A female patient 70 years of age; the chart notes prior malignancy (patient or family), tobacco use, no prior skin cancer (patient or family), and no alcohol use; a clinical photograph of a skin lesion; the patient is FST II — 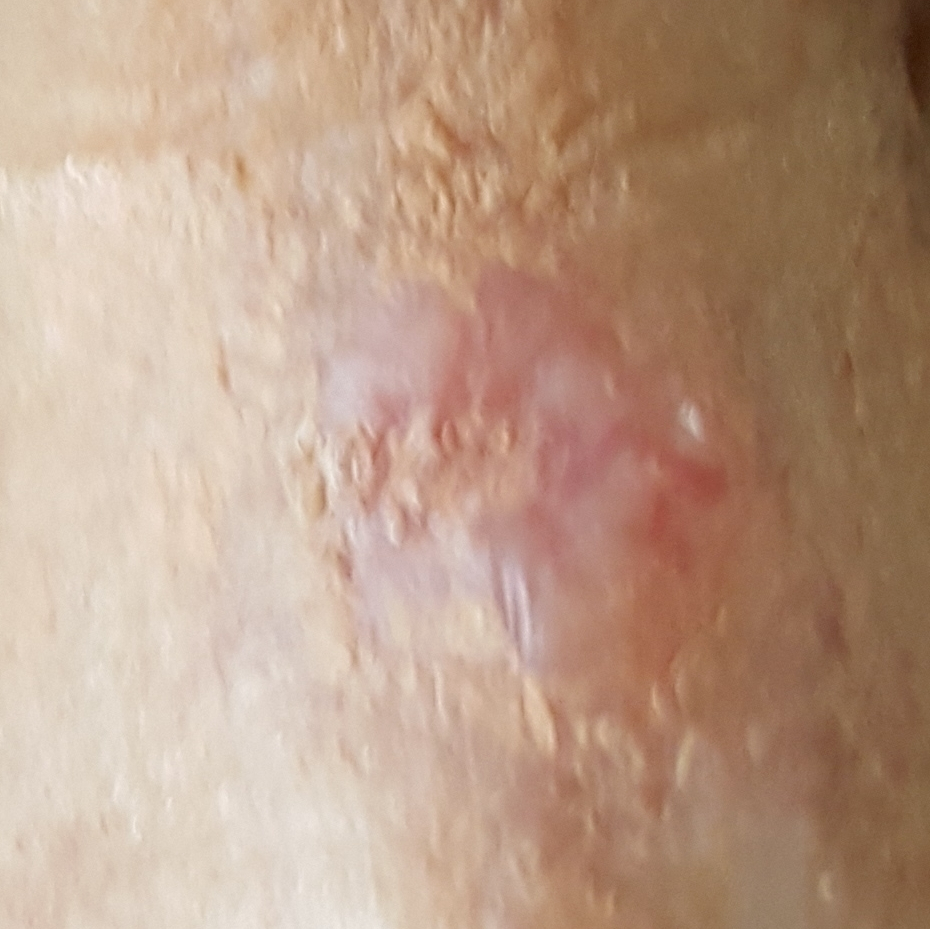Located on the face.
The lesion measures 12 × 9 mm.
By the patient's account, the lesion itches, is elevated, and has grown.
Confirmed on histopathology as a skin cancer — a basal cell carcinoma.